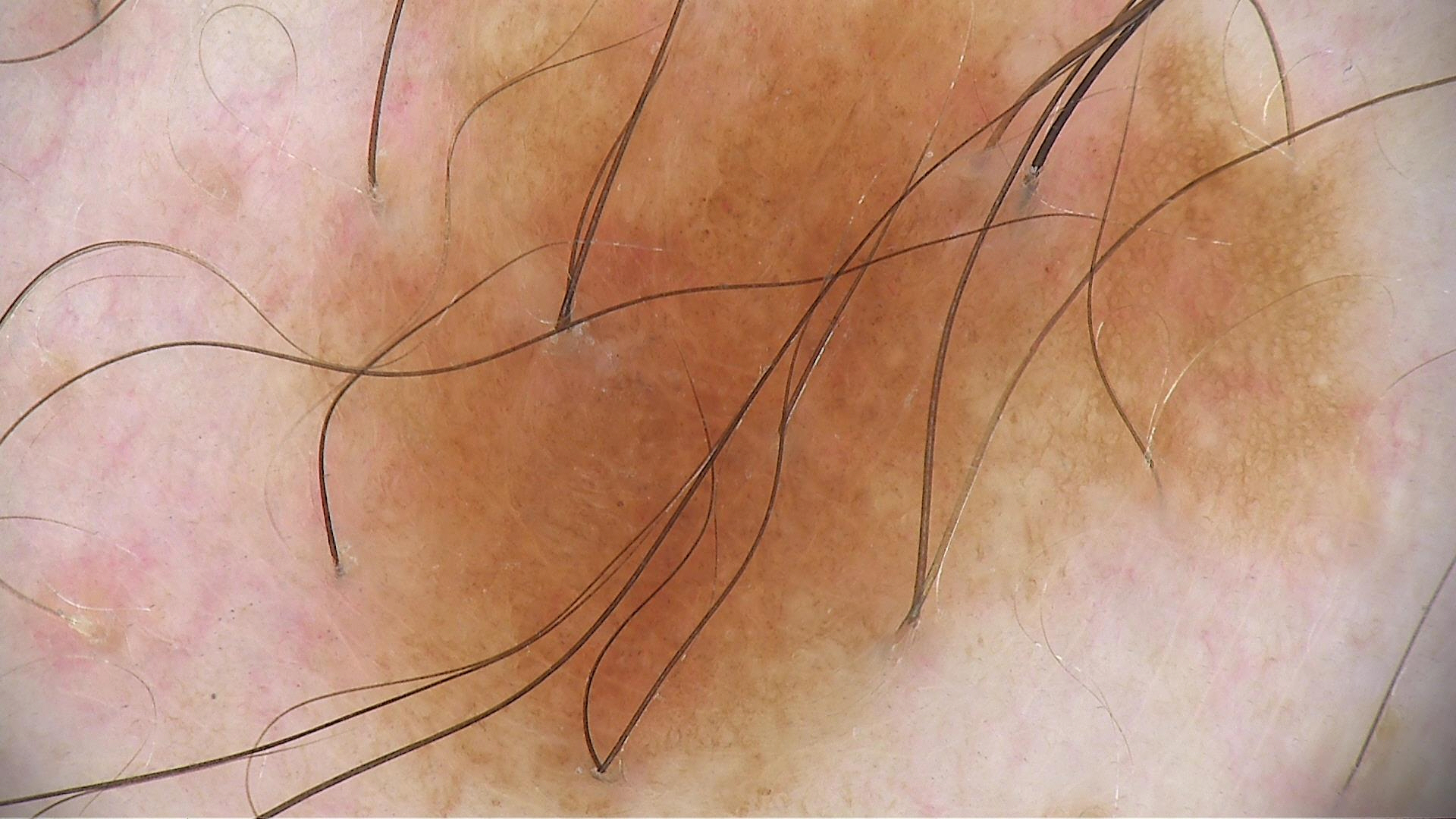A dermoscopy image of a single skin lesion. Diagnosed as a benign lesion — a dysplastic junctional nevus.